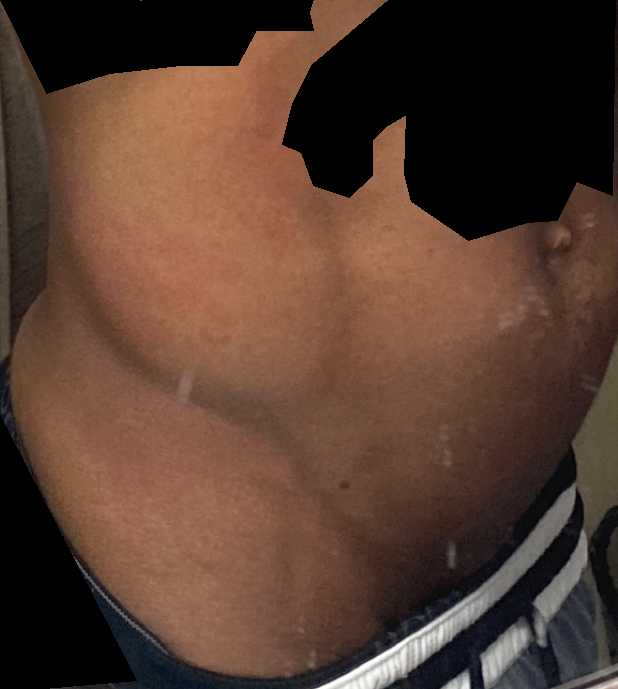assessment: no skin condition identified | onset: one to three months | skin tone: lay reviewers estimated Monk Skin Tone 4 or 5 (two reviewer pools) | surface texture: flat and raised or bumpy | site: arm, palm, head or neck and back of the hand | subject: male, age 30–39 | shot type: at an angle | patient's own categorization: a rash | systemic symptoms: none reported.